A dermoscopic photograph of a skin lesion.
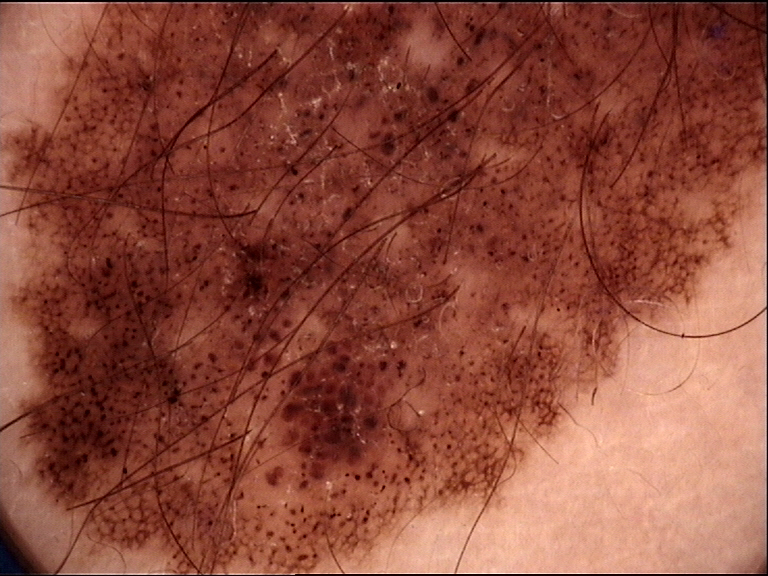The morphology is that of a banal lesion. The diagnostic label was a congenital compound nevus.